This is a dermoscopic photograph of a skin lesion — 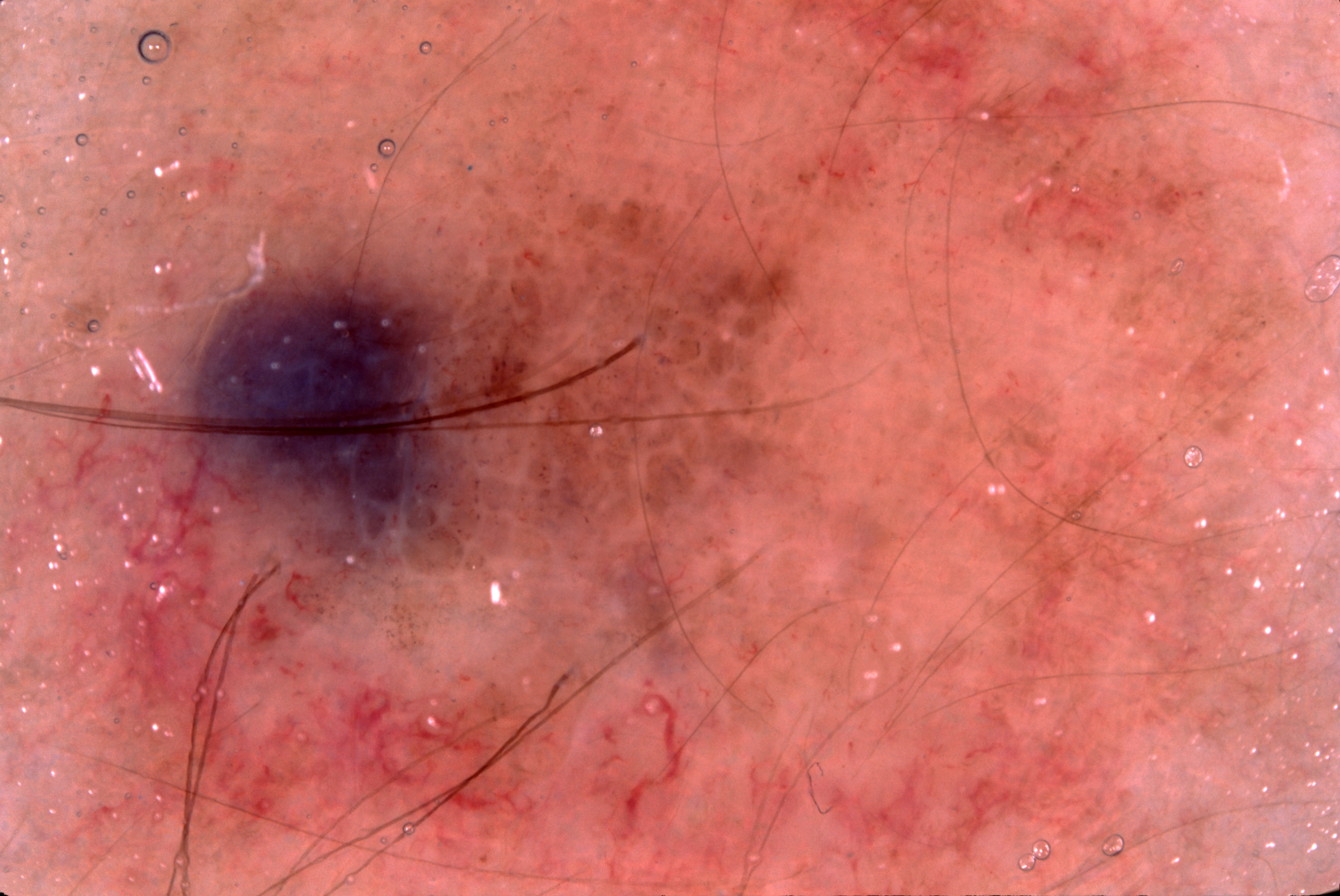The lesion reaches across nearly the entire image.
Dermoscopic examination shows negative network; no pigment network, streaks, or milia-like cysts.
Expert review diagnosed this as a melanocytic nevus, a benign lesion.